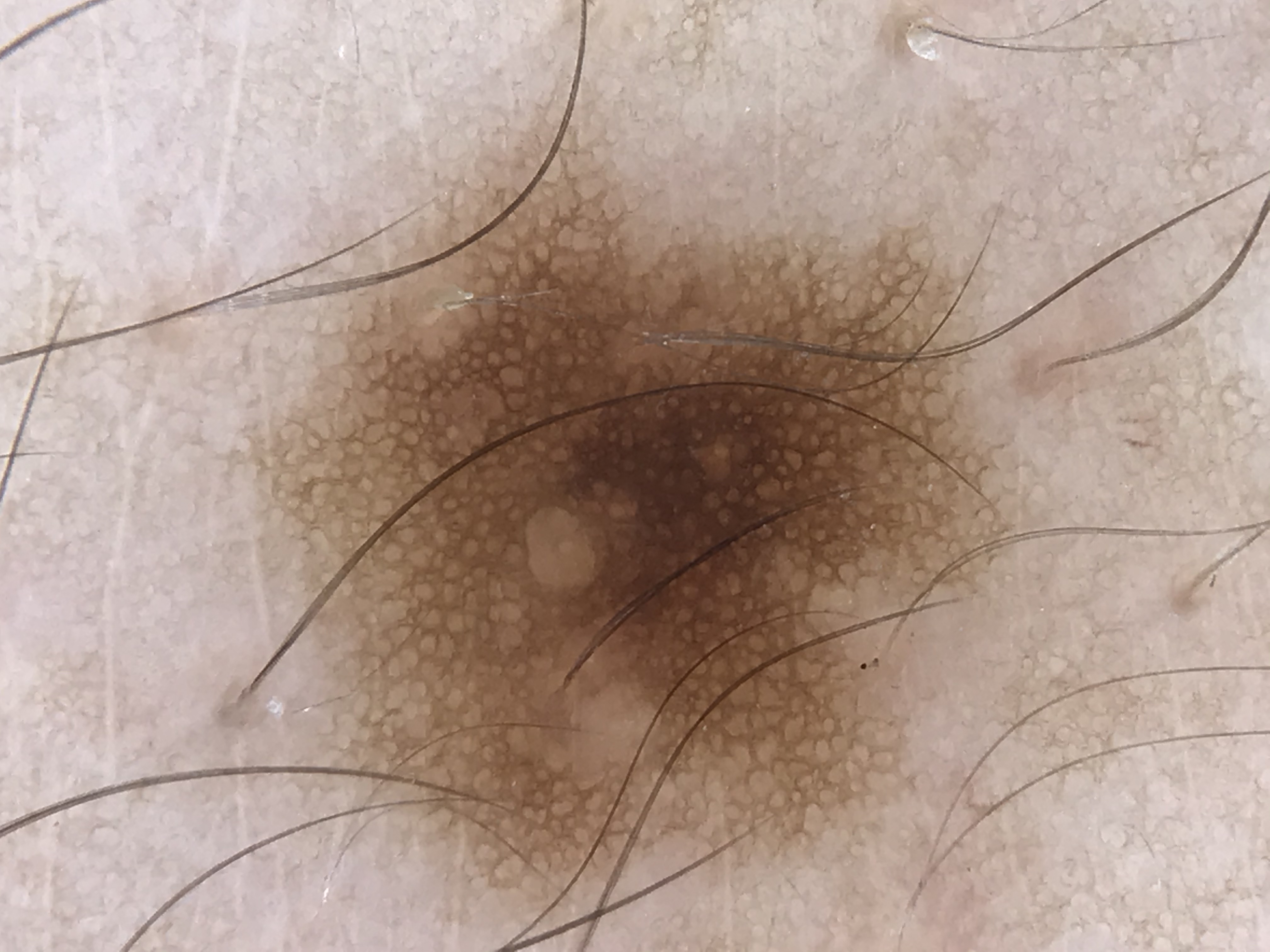Summary:
A dermoscopic photograph of a skin lesion. The morphology is that of a banal lesion.
Conclusion:
Consistent with a junctional nevus.